The photo was captured at a distance.
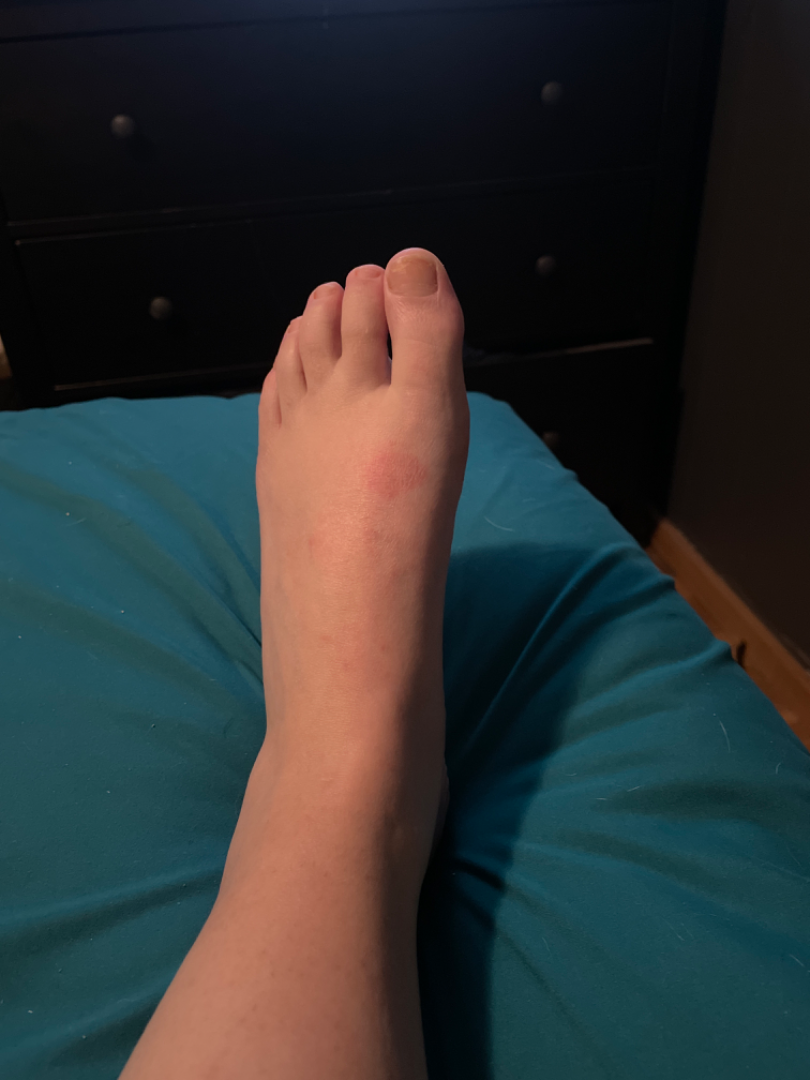Skin tone: Fitzpatrick IV.
On photographic review: the differential is split between Lichen Simplex Chronicus, Allergic Contact Dermatitis and Irritant Contact Dermatitis.